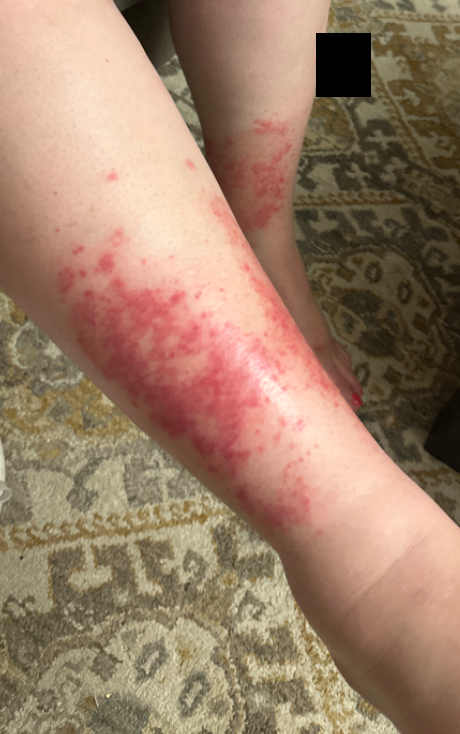assessment = could not be assessed
shot type = at a distance